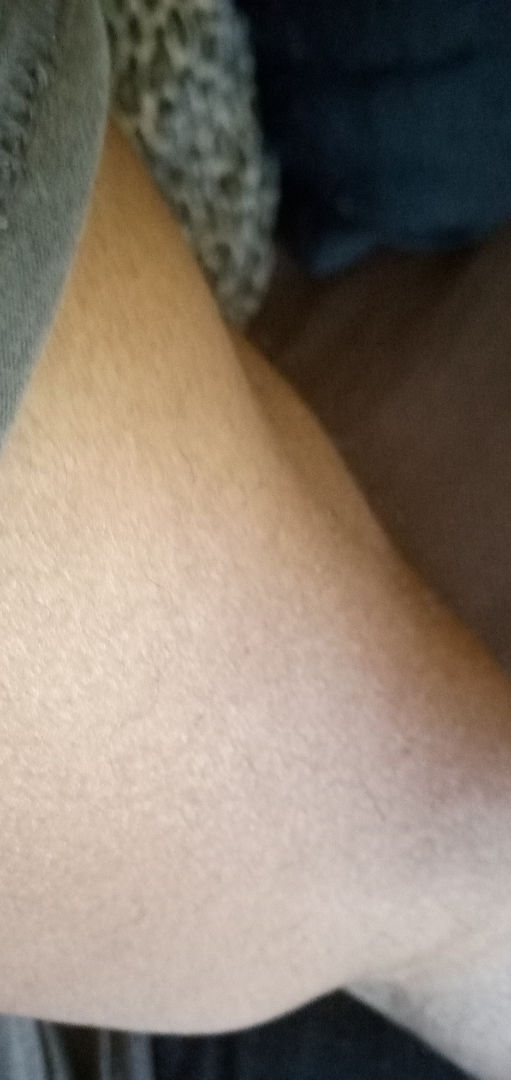Review:
No differential diagnosis could be assigned on photographic review.
Patient information:
The lesion is described as rough or flaky. Fitzpatrick V. The patient described the issue as a pigmentary problem. Reported duration is since childhood. Located on the arm. The lesion is associated with darkening. This is a close-up image.